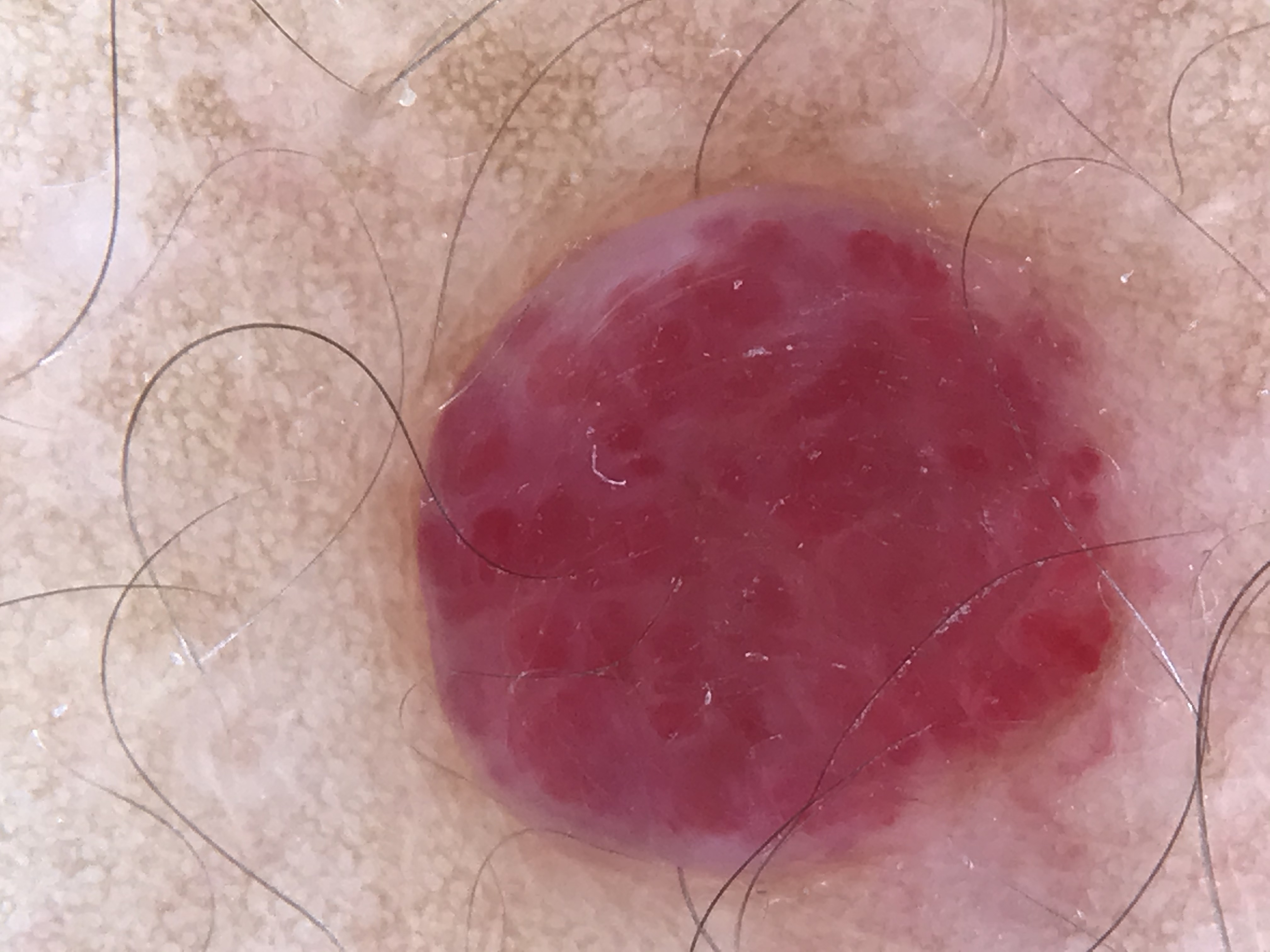Findings:
– category · vascular
– diagnostic label · hemangioma (expert consensus)